Self-categorized by the patient as a rash · the lesion involves the arm · the patient notes itching · reported duration is one to three months · texture is reported as raised or bumpy · this image was taken at an angle:
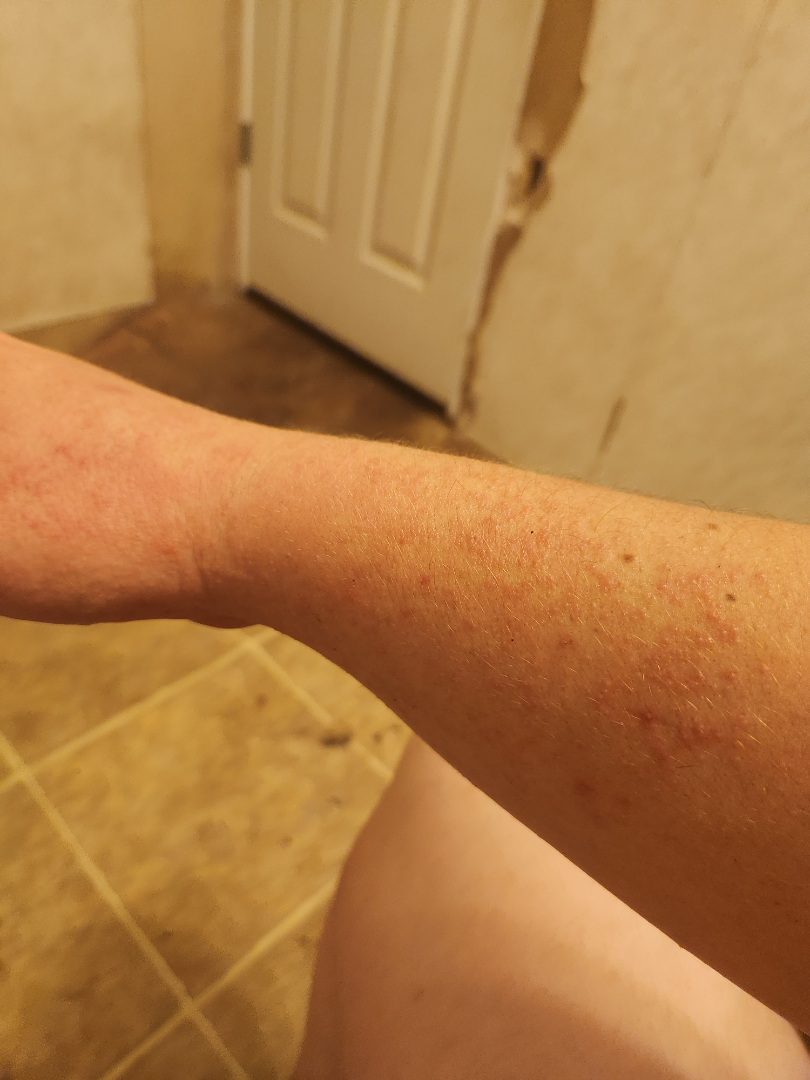Review: On remote dermatologist review: Allergic Contact Dermatitis (54%); Drug Rash (23%); Viral Exanthem (23%).